A dermoscopy image of a single skin lesion.
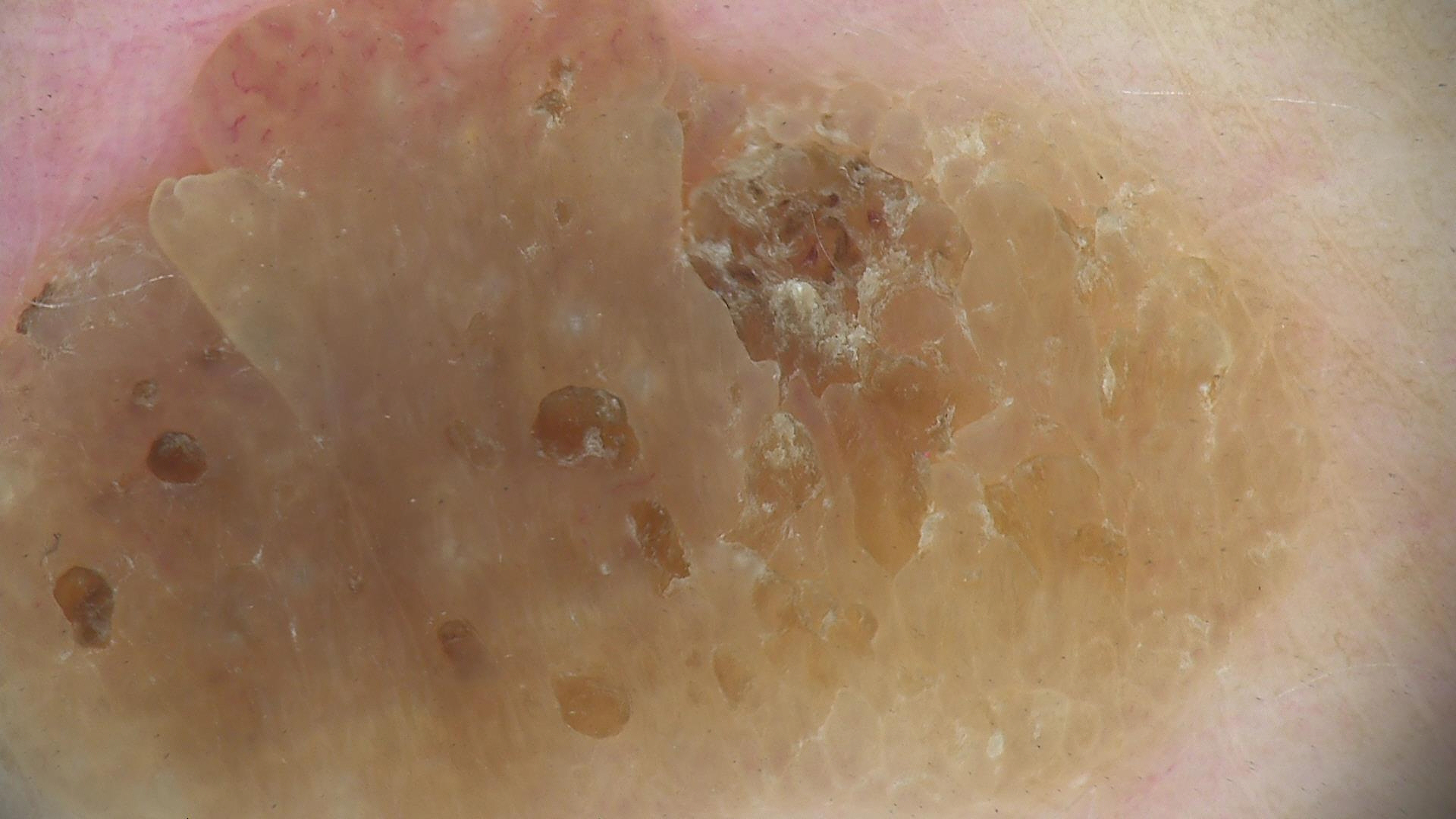Q: How is the lesion classified?
A: keratinocytic
Q: What is the diagnosis?
A: seborrheic keratosis (expert consensus)